The leg is involved, this is a close-up image, present for about one day, the lesion is described as flat, the patient described the issue as a rash, the lesion is associated with burning and itching.
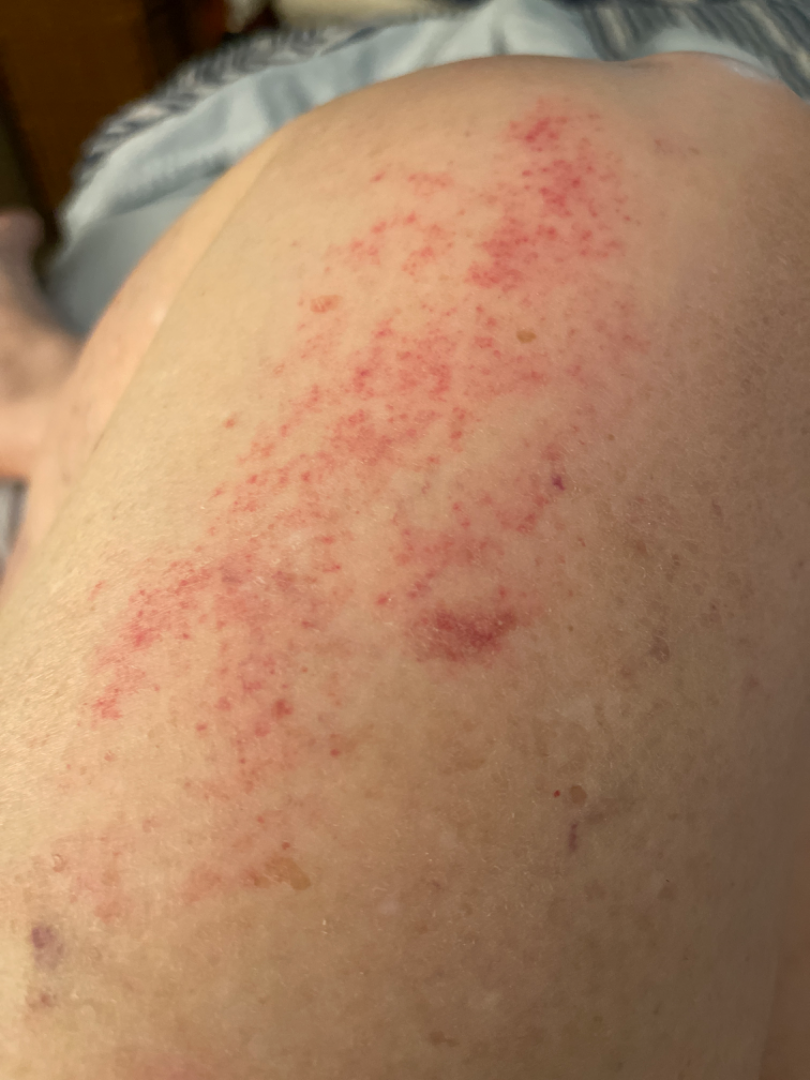Findings:
The case was difficult to assess from the available photograph.